Dermoscopy of a skin lesion: 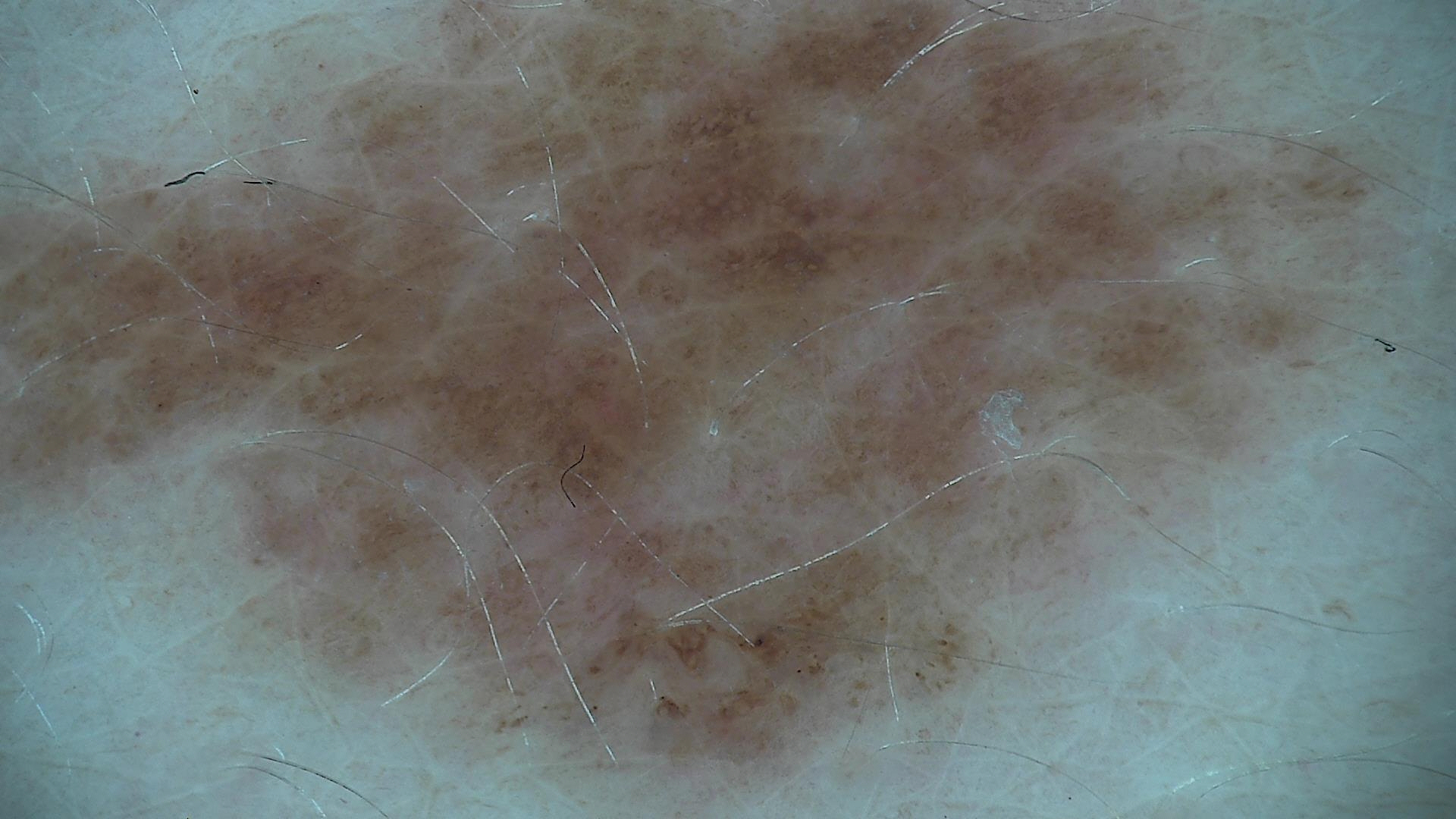{
  "diagnosis": {
    "name": "dysplastic junctional nevus",
    "code": "jd",
    "malignancy": "benign",
    "super_class": "melanocytic",
    "confirmation": "expert consensus"
  }
}